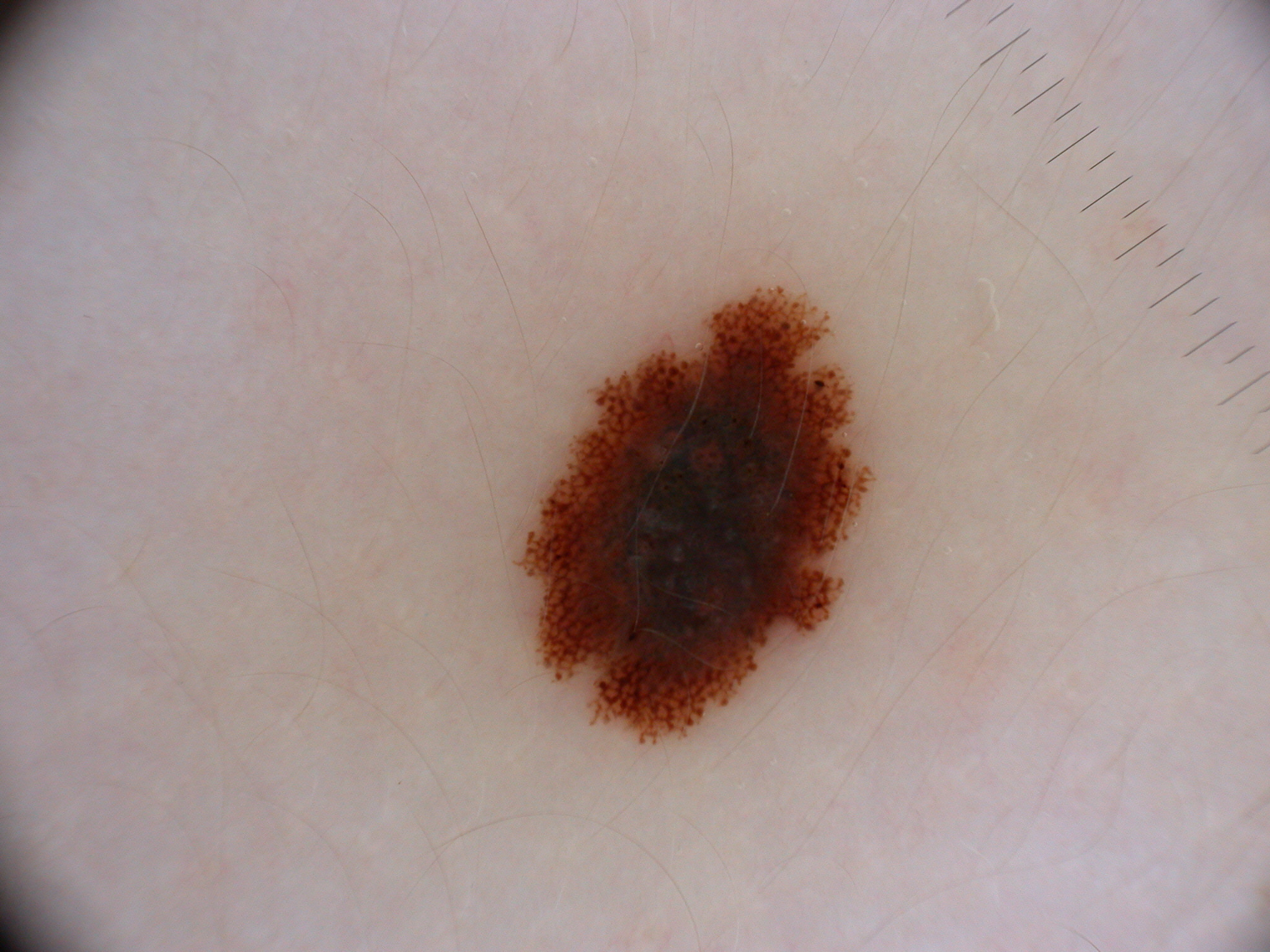imaging = dermoscopic image | dermoscopic findings = pigment network and globules; absent: negative network, streaks, and milia-like cysts | lesion bbox = [512,286,875,743] | assessment = a melanocytic nevus, a benign lesion.